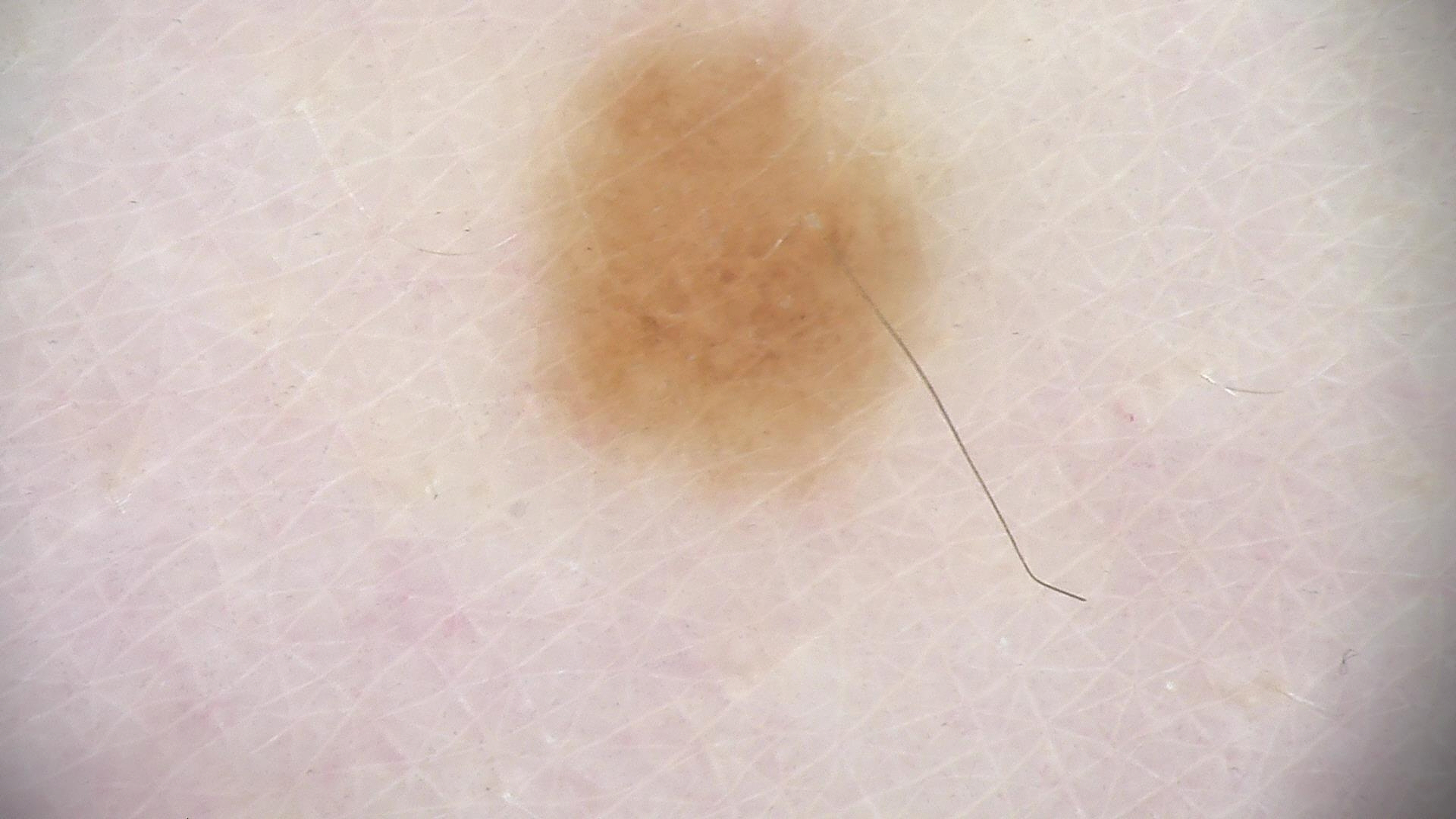Findings: Dermoscopy of a skin lesion. Conclusion: The diagnostic label was a benign lesion — a dysplastic junctional nevus.